A dermoscopic view of a skin lesion:
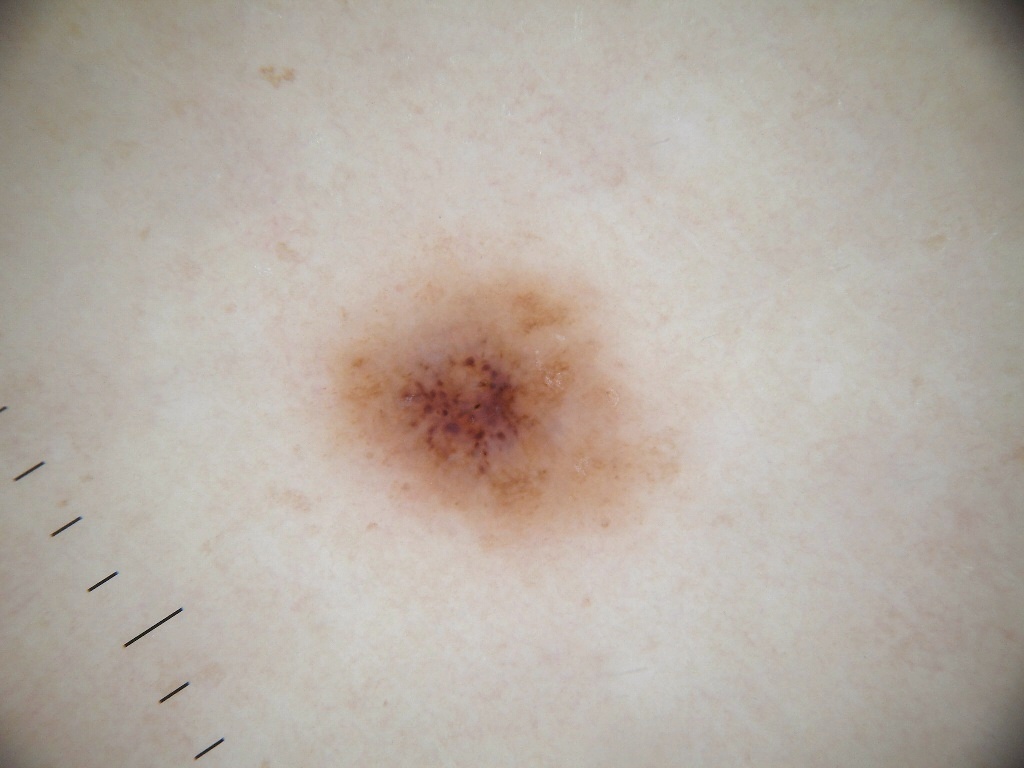bounding box: x1=304 y1=229 x2=678 y2=555
features: globules
diagnosis: a melanocytic nevus